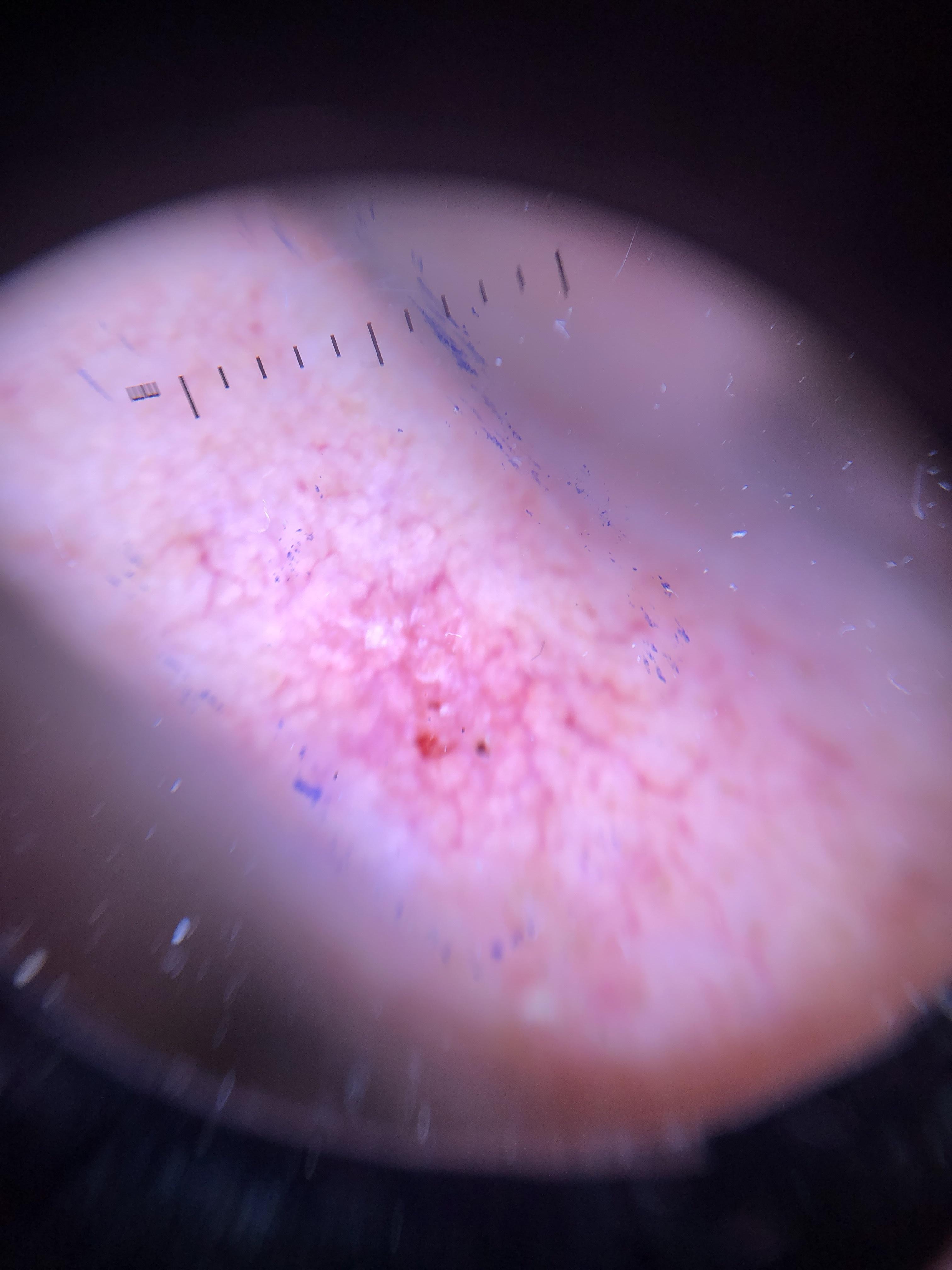A male subject approximately 75 years of age. Recorded as Fitzpatrick phototype I. Dermoscopy of a skin lesion. The clinical assessment was a solar or actinic keratosis.